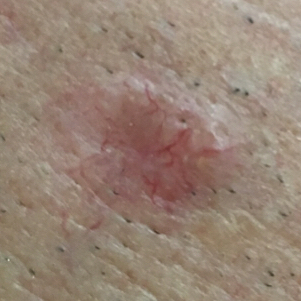image: clinical photo
risk_factors:
  positive:
    - pesticide exposure
    - prior cancer (patient or family)
patient:
  age: 62
  gender: male
skin_type: II
lesion_location: the face
lesion_size:
  diameter_1_mm: 10.0
  diameter_2_mm: 7.0
symptoms:
  present:
    - itching
    - elevation
diagnosis:
  name: basal cell carcinoma
  code: BCC
  malignancy: malignant
  confirmation: histopathology